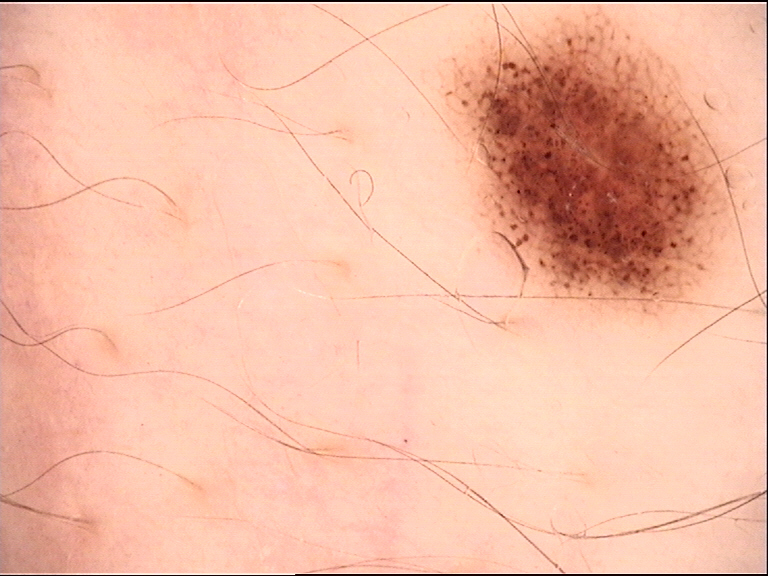Q: What is the imaging modality?
A: dermoscopy
Q: What is this lesion?
A: dysplastic junctional nevus (expert consensus)